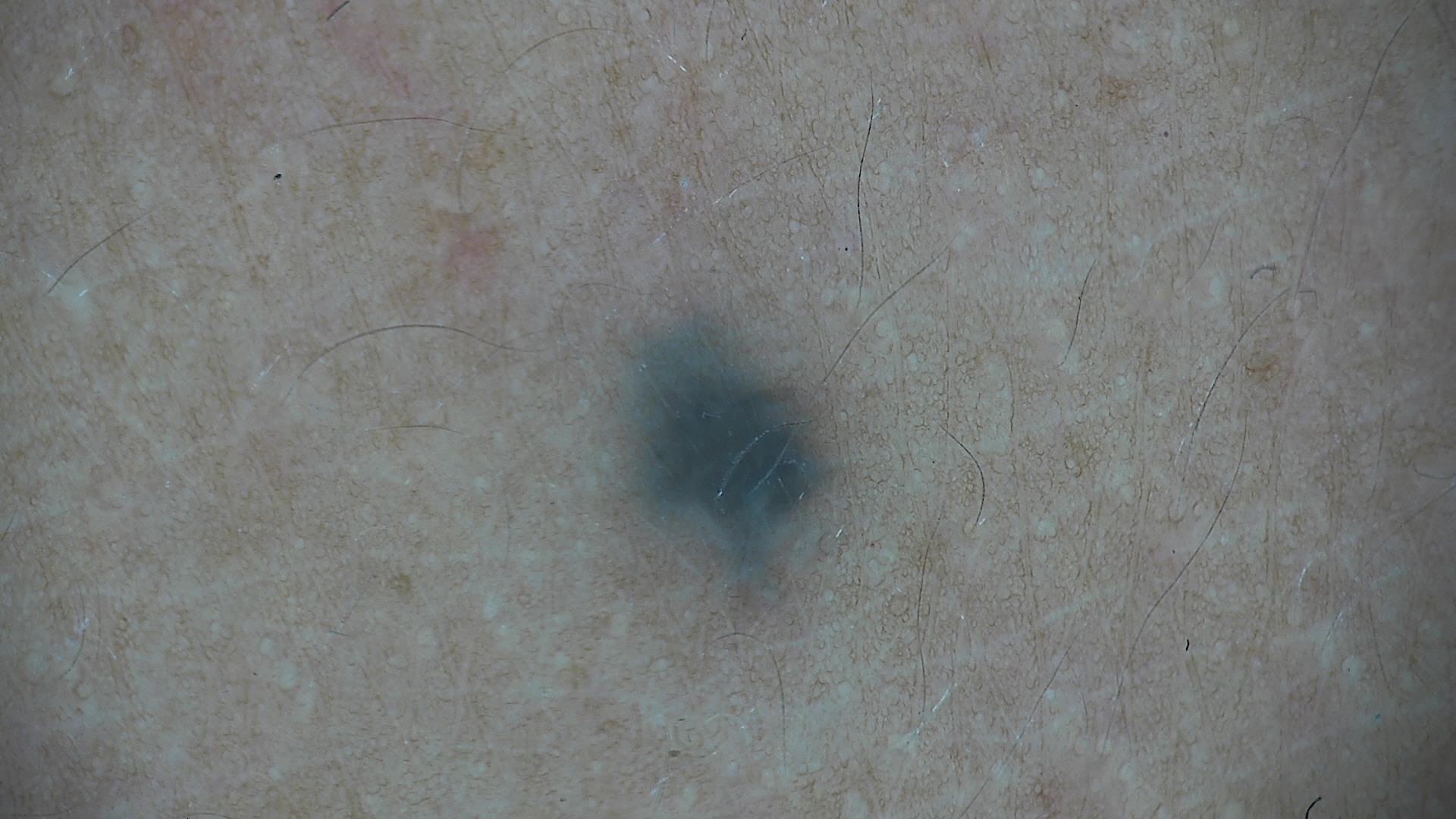modality = dermatoscopy
subtype = dermal, banal
class = blue nevus (expert consensus)